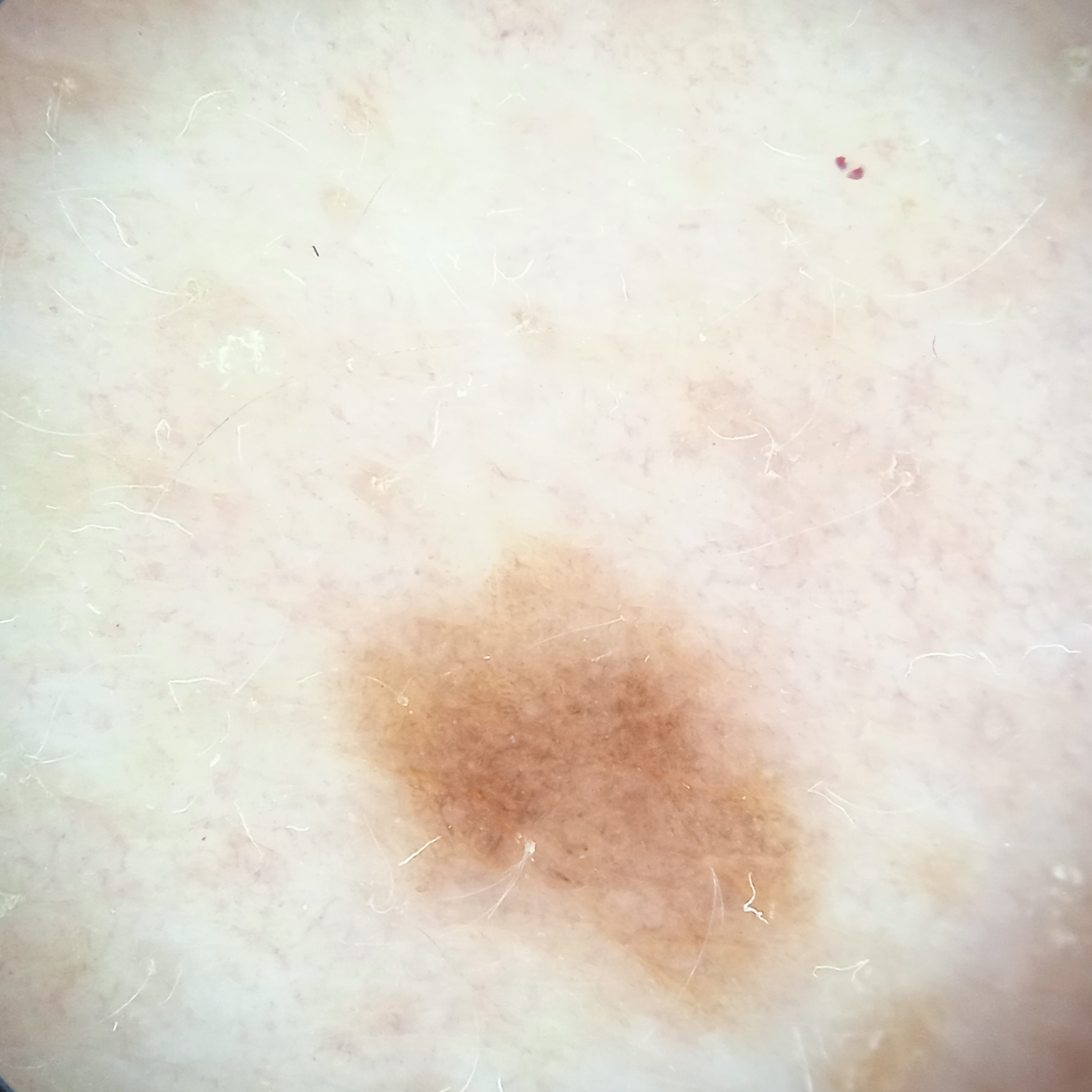Findings:
The patient describes having a moderate number of moles. On a questionnaire the patient reported a prior organ transplant and immunosuppression. A female patient aged 55. Collected as part of a research study, without a referral diagnosis. Dermoscopy of a skin lesion. The patient says their skin reddens painfully with sun exposure. The lesion involves the back. The lesion measures approximately 6.3 mm.
Assessment:
The diagnostic impression was a melanocytic nevus.